Present for one to four weeks, the patient is a female aged 18–29, the contributor reports associated fatigue and joint pain, the lesion involves the leg, this is a close-up image, symptoms reported: bothersome appearance and enlargement — 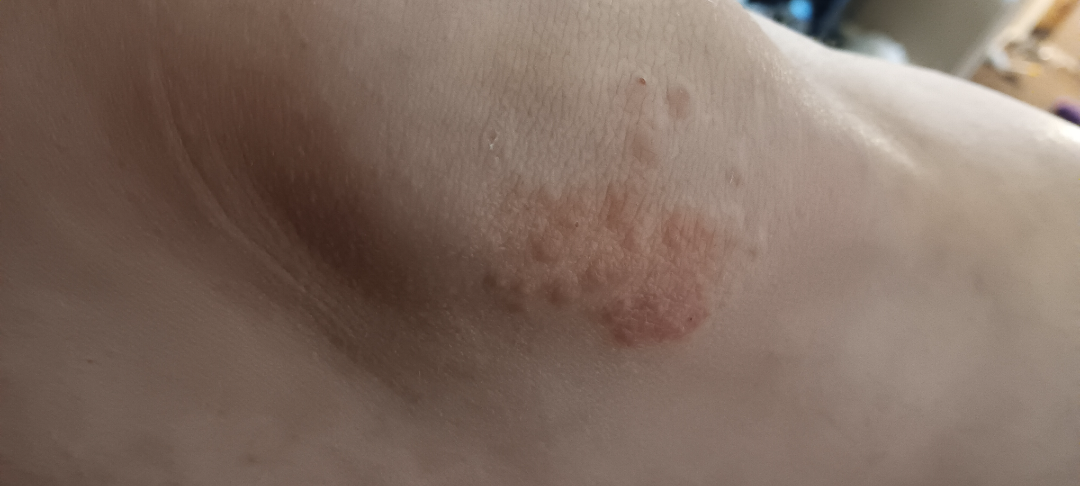Notes:
• assessment — the primary impression is Psoriasis